The subject is a female aged around 60, a dermoscopic view of a skin lesion: 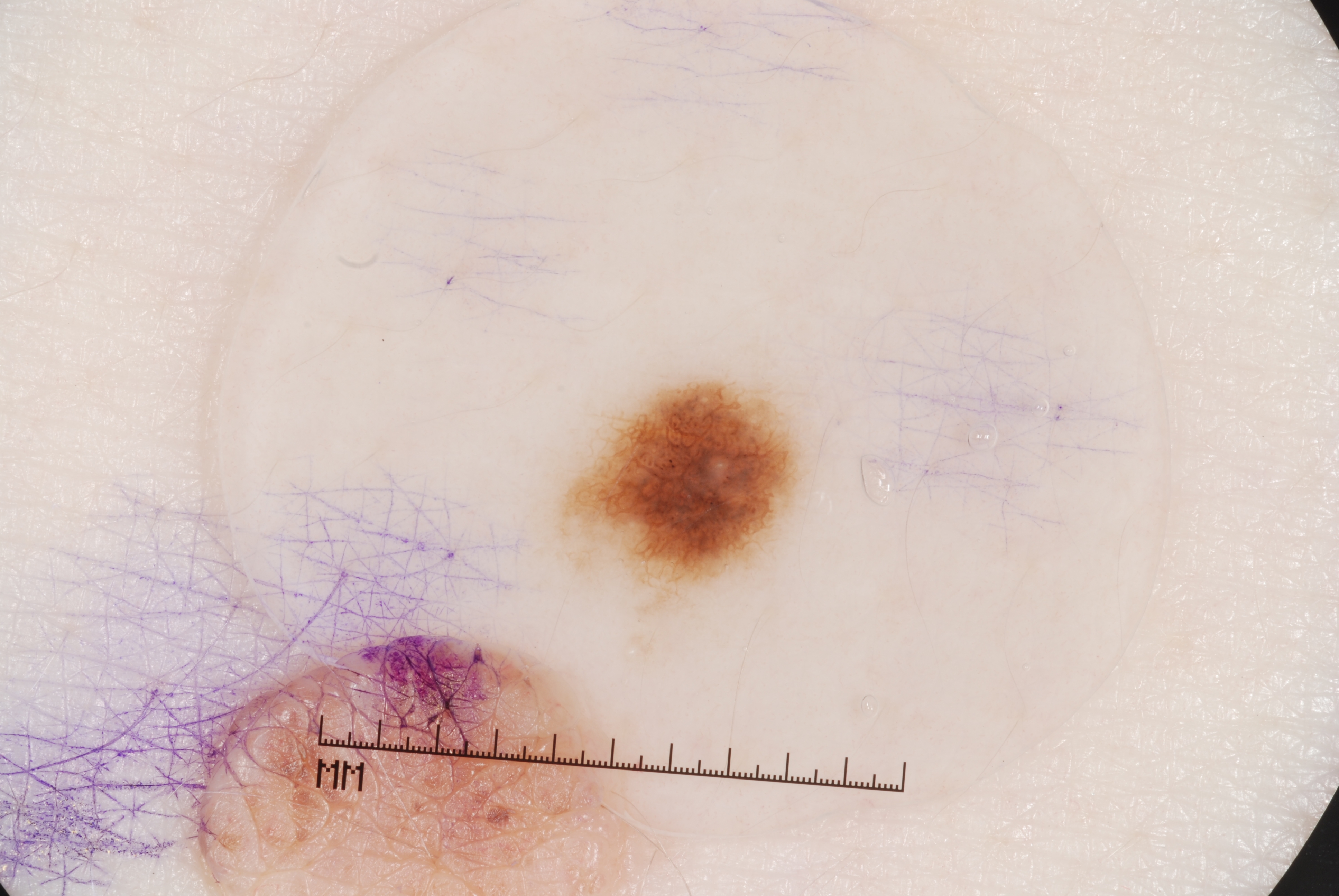Dermoscopic review identifies pigment network and milia-like cysts, with no streaks or negative network.
As (left, top, right, bottom), lesion location: <box>552, 373, 812, 617</box>.
The lesion covers approximately 4% of the dermoscopic field.
The diagnostic assessment was a melanocytic nevus.